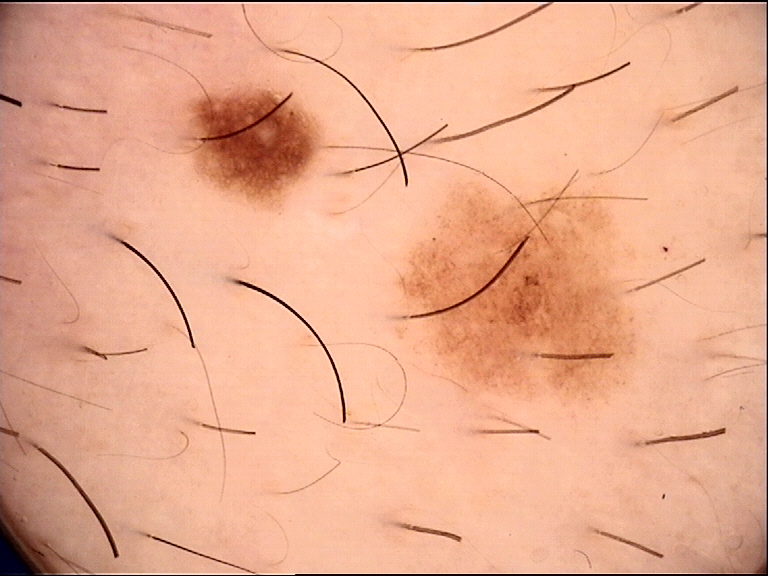A skin lesion imaged with a dermatoscope. The diagnosis was a benign lesion — a dysplastic junctional nevus.